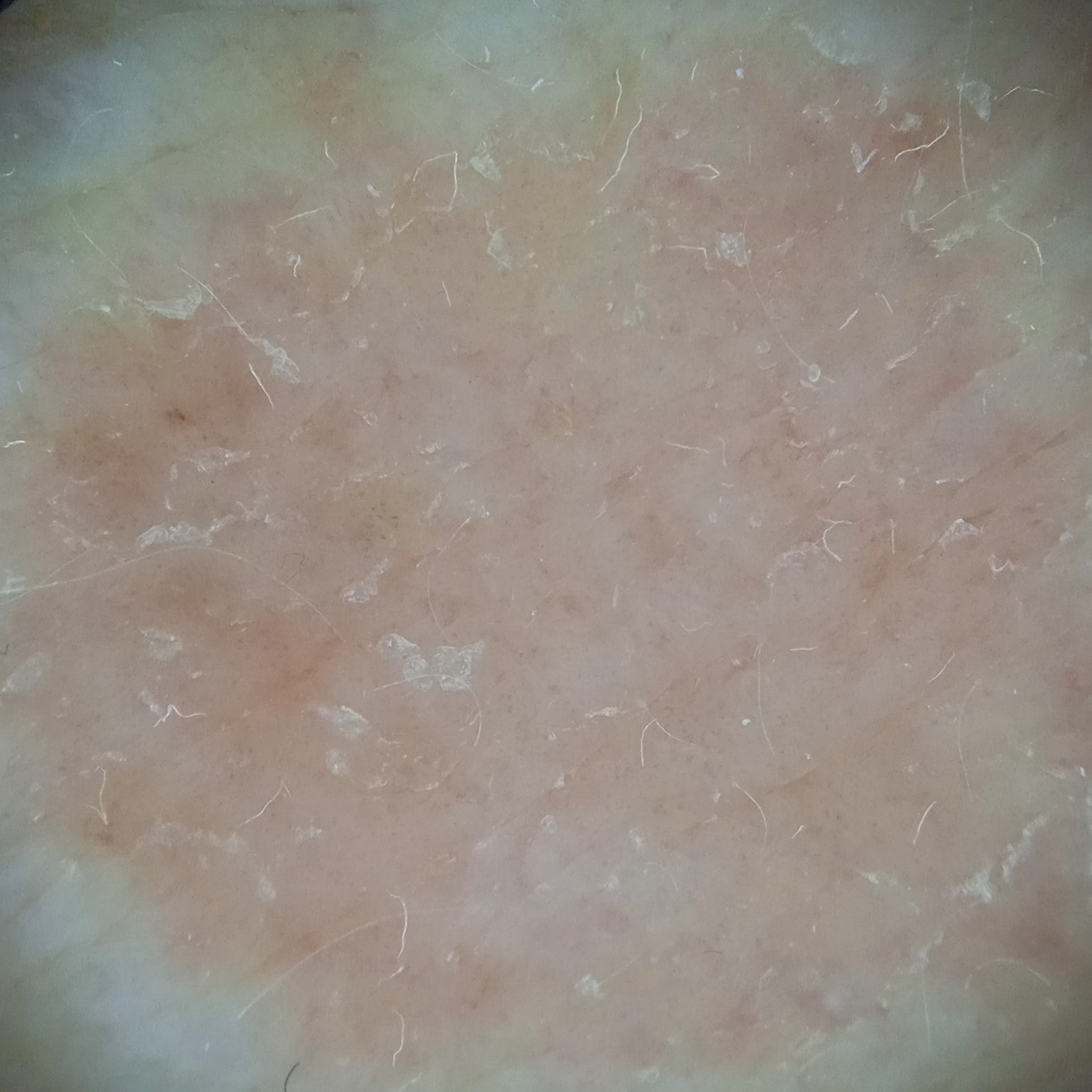Findings:
– assessment: basal cell carcinoma (dermatologist consensus)